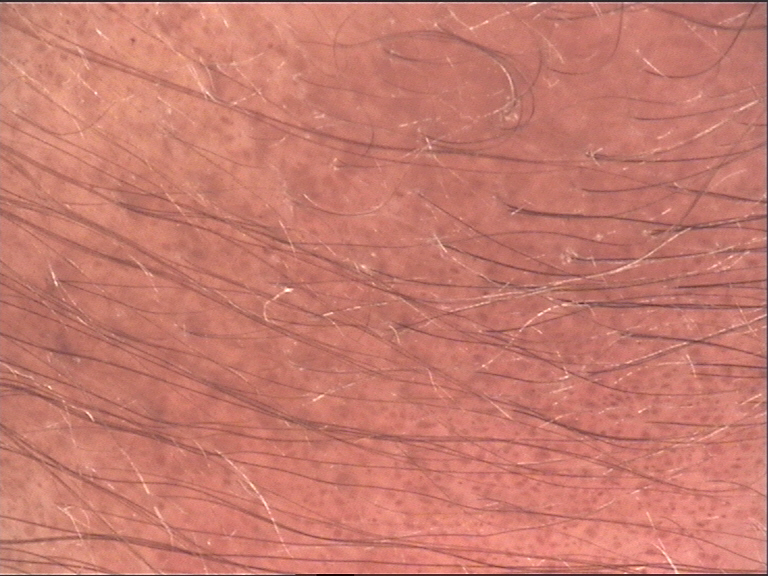A skin lesion imaged with a dermatoscope. The morphology is that of a banal lesion. Diagnosed as a congenital junctional nevus.